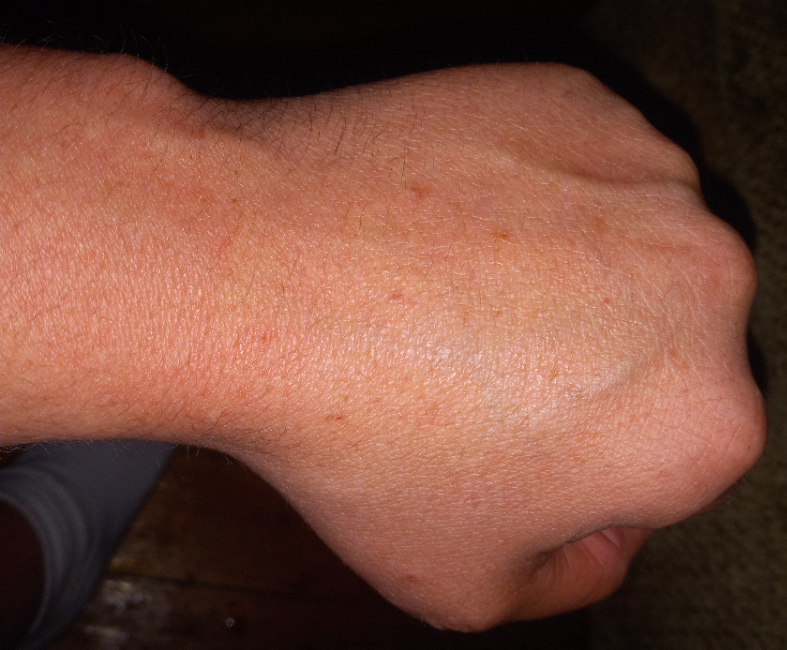Review:
Diagnostic features were not clearly distinguishable in this photograph.
Patient information:
This is a close-up image. The affected area is the leg, arm, sole of the foot, back of the hand and top or side of the foot.